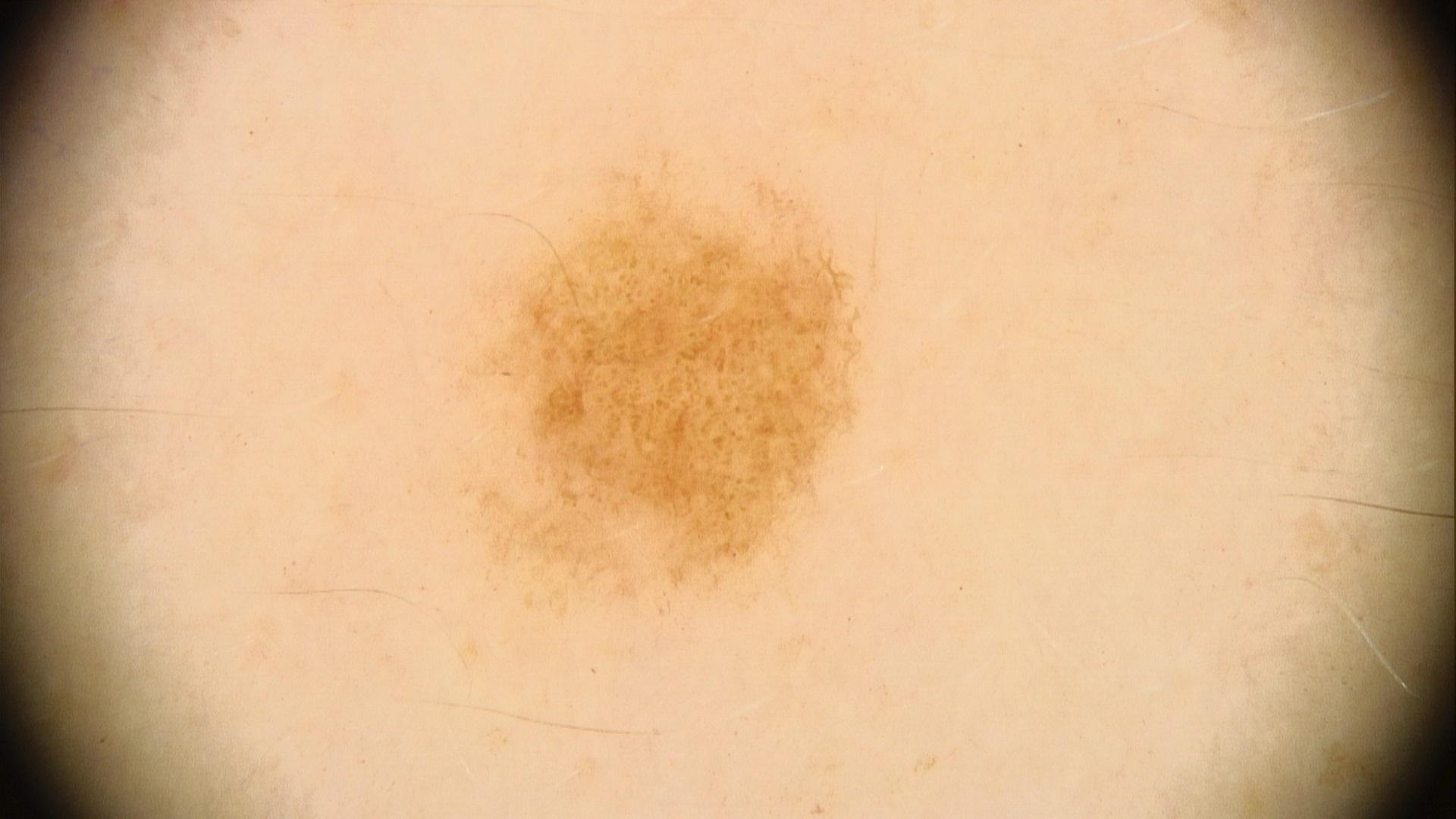Per the chart, melanoma in a first-degree relative.
The lesion was found on the trunk.
Consistent with a lesion of melanocytic origin — a nevus.